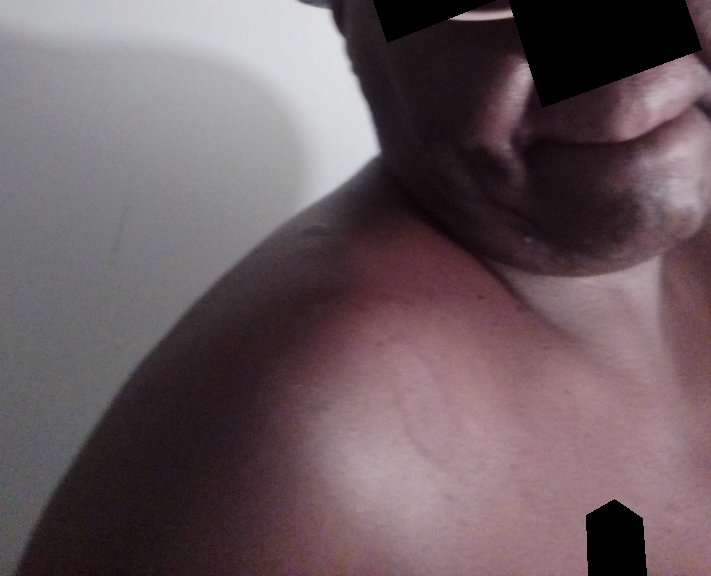assessment=indeterminate; site=back of the hand, leg and arm; framing=at an angle.